The lesion involves the arm, the patient is a female aged 40–49, the photograph was taken at a distance: 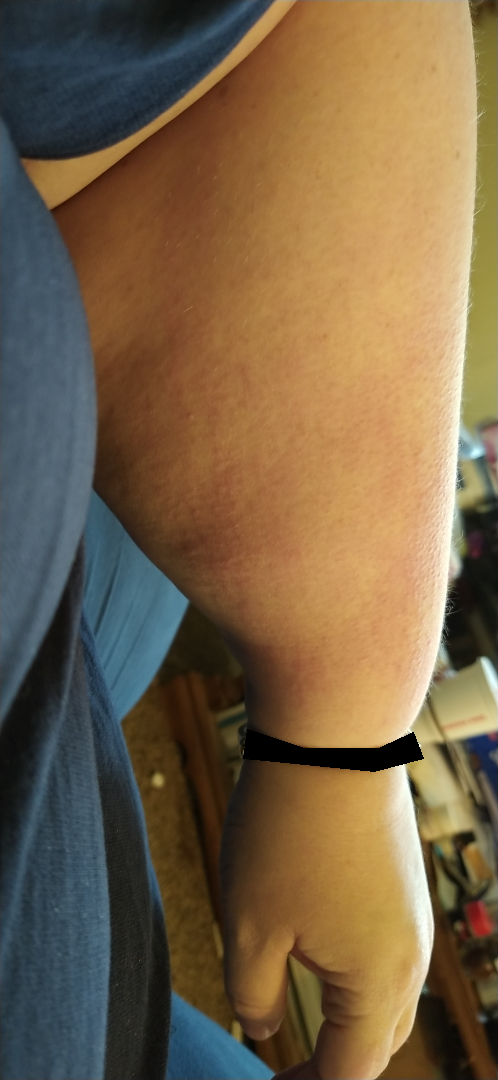lesion texture = raised or bumpy | self-categorized as = a rash | duration = more than one year | other reported symptoms = mouth sores, joint pain and fatigue | patient-reported symptoms = itching and darkening | skin tone = Fitzpatrick II; lay graders estimated Monk skin tone scale 3 | clinical impression = Eczema (most likely); Acute dermatitis, NOS (possible); Allergic Contact Dermatitis (unlikely); Viral Exanthem (unlikely); Keratosis pilaris (unlikely).